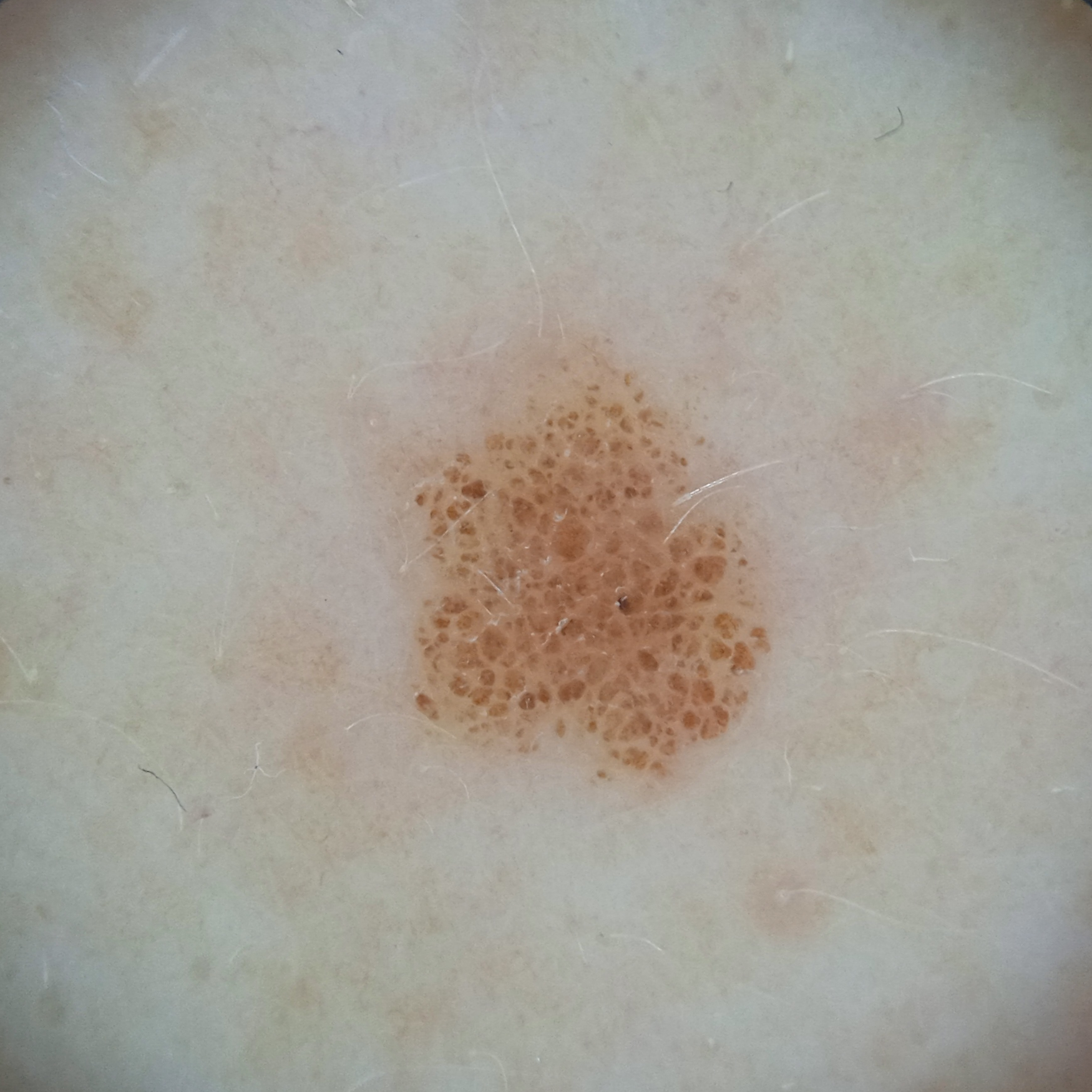Q: What kind of image is this?
A: dermoscopy
Q: Why was this imaged?
A: research study (no referral diagnosis)
Q: Patient demographics?
A: female, 50 years of age
Q: Where is the lesion?
A: the back
Q: How large is the lesion?
A: 5.1 mm
Q: What was the diagnosis?
A: melanocytic nevus (dermatologist consensus)